A dermatoscopic image of a skin lesion.
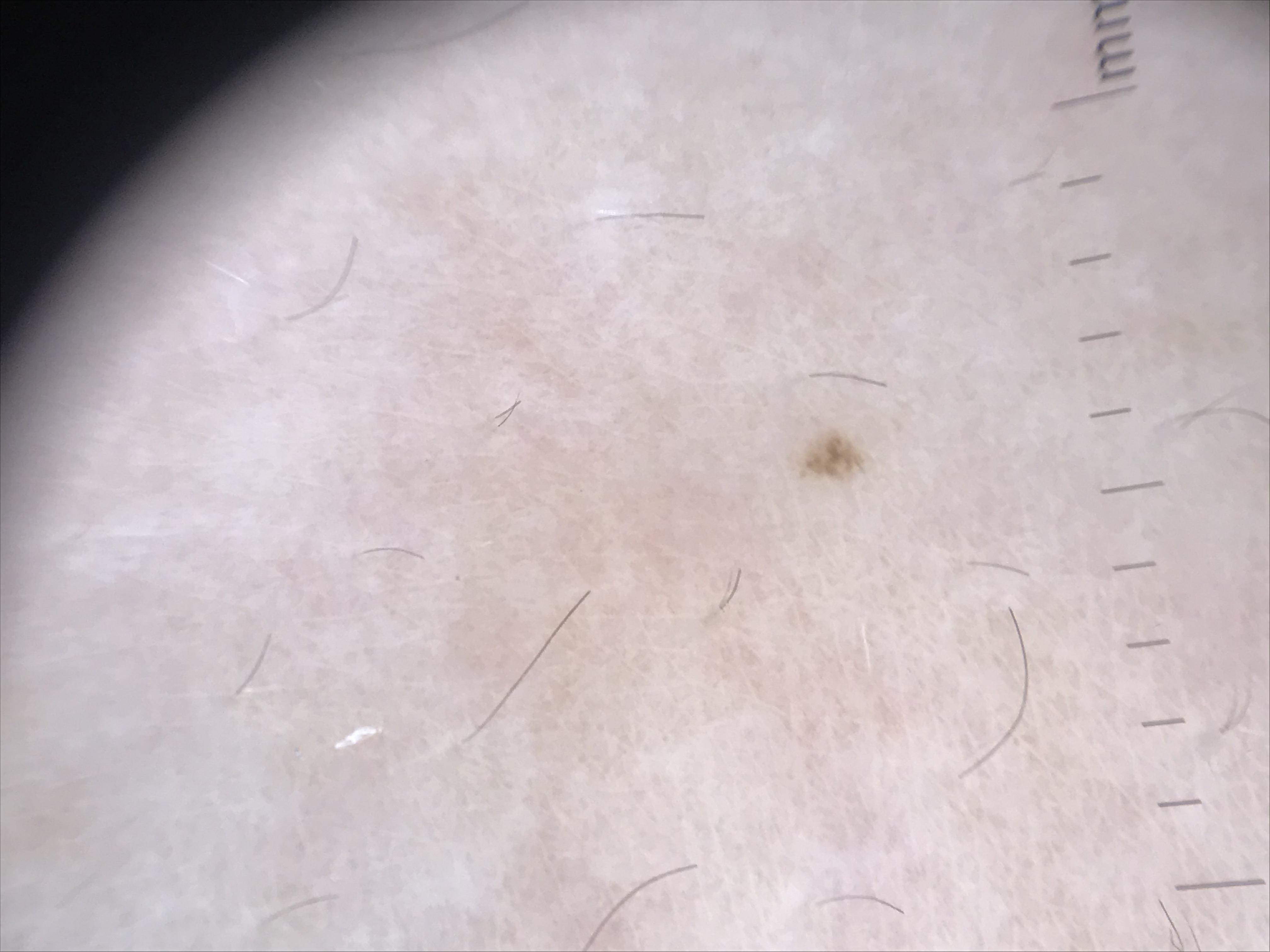The diagnosis was a banal lesion — a junctional nevus.